Human graders estimated Monk Skin Tone 3 (US pool) or 2 (India pool), an image taken at an angle:
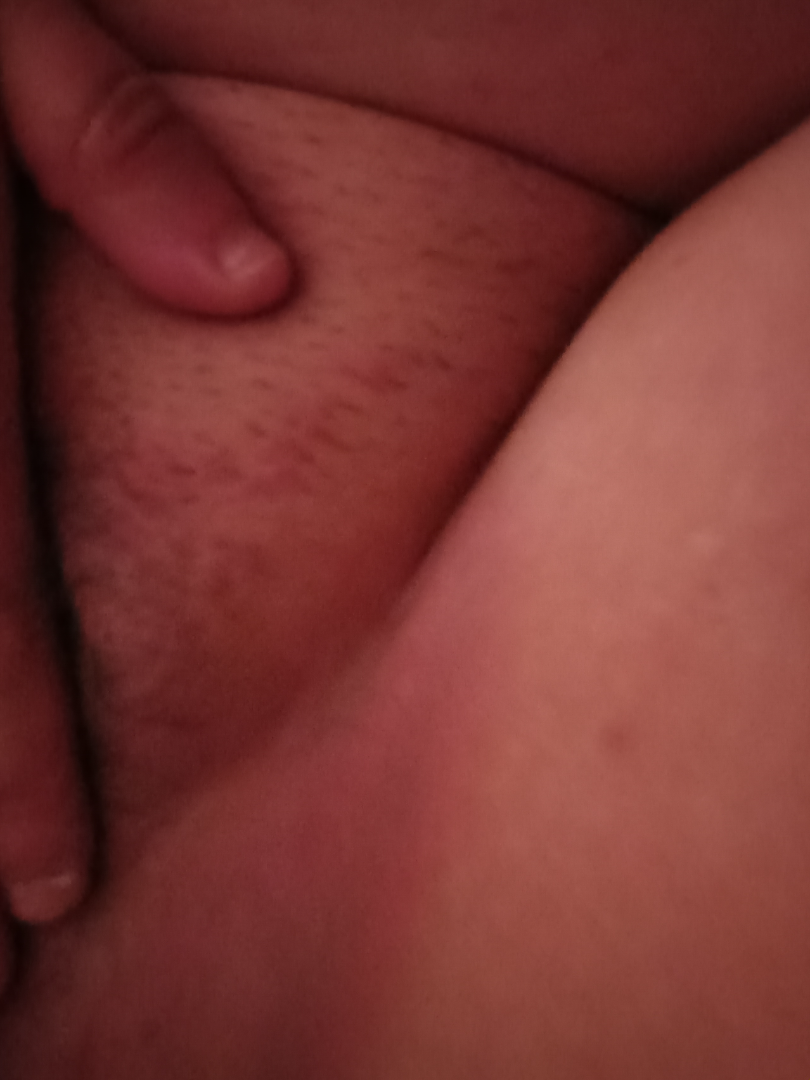Q: What was the assessment?
A: could not be assessed